Close-up view: 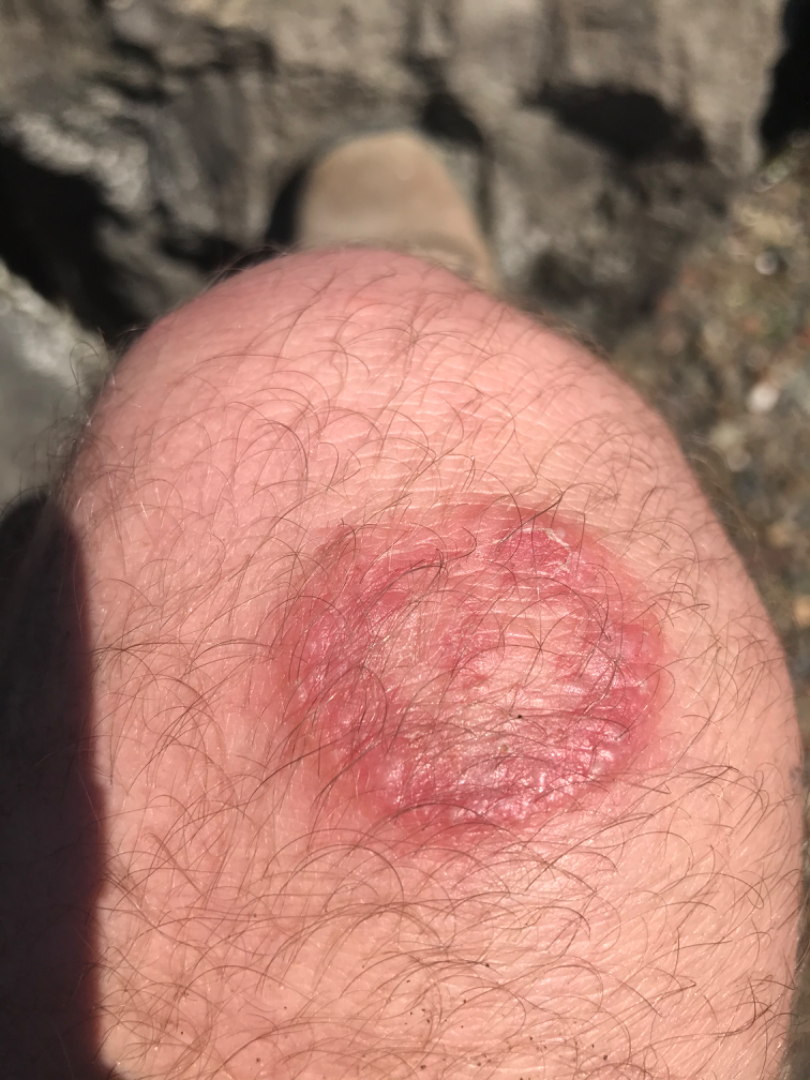| feature | finding |
|---|---|
| differential | one reviewing dermatologist: the favored diagnosis is Allergic Contact Dermatitis; also consider Irritant Contact Dermatitis |